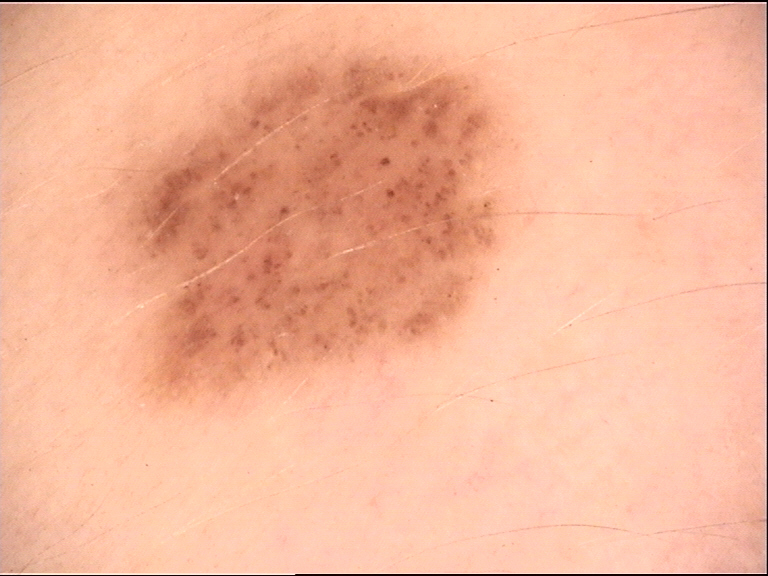Summary: A dermoscopic close-up of a skin lesion. Impression: Classified as a dysplastic junctional nevus.